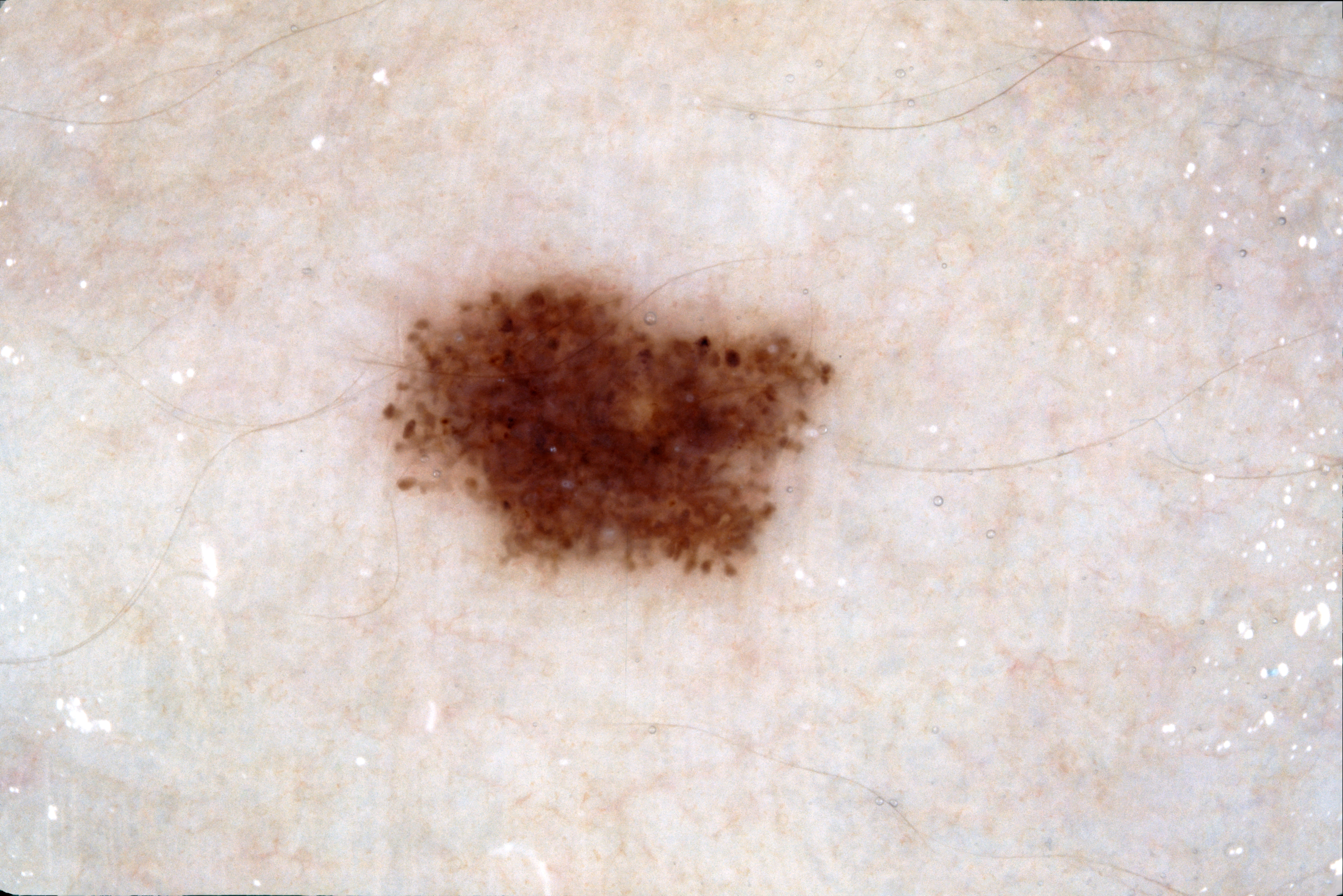{"image": {"modality": "dermoscopy"}, "patient": {"sex": "female", "age_approx": 60}, "lesion_location": {"bbox_xyxy": [381, 270, 839, 579]}, "lesion_extent": {"approx_field_fraction_pct": 8}, "dermoscopic_features": {"present": ["streaks"], "absent": ["milia-like cysts", "negative network", "pigment network"]}, "diagnosis": {"name": "melanocytic nevus", "malignancy": "benign", "lineage": "melanocytic", "provenance": "clinical"}}